A female subject aged 23 to 27. A dermoscopic image of a skin lesion.
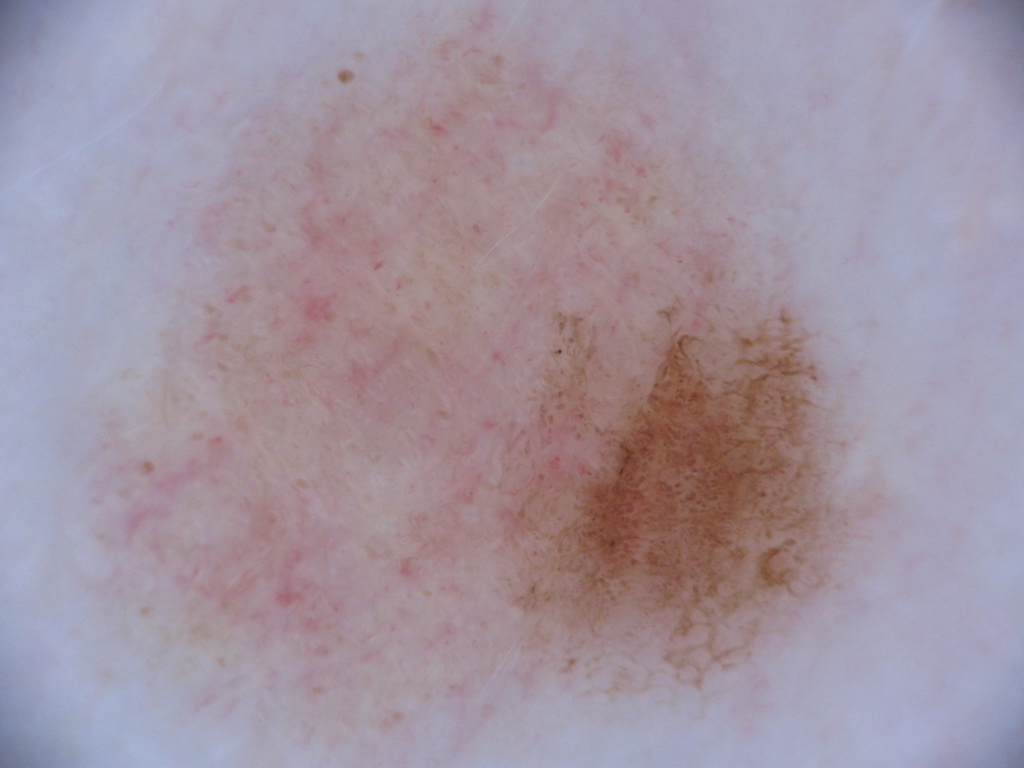Case summary: The lesion extends to the edge of the dermoscopic field. Dermoscopic review identifies globules and pigment network. With coordinates (x1, y1, x2, y2), the visible lesion spans [105,0,885,727]. Impression: The lesion was assessed as a melanocytic nevus, a benign skin lesion.